A dermoscopic image of a skin lesion:
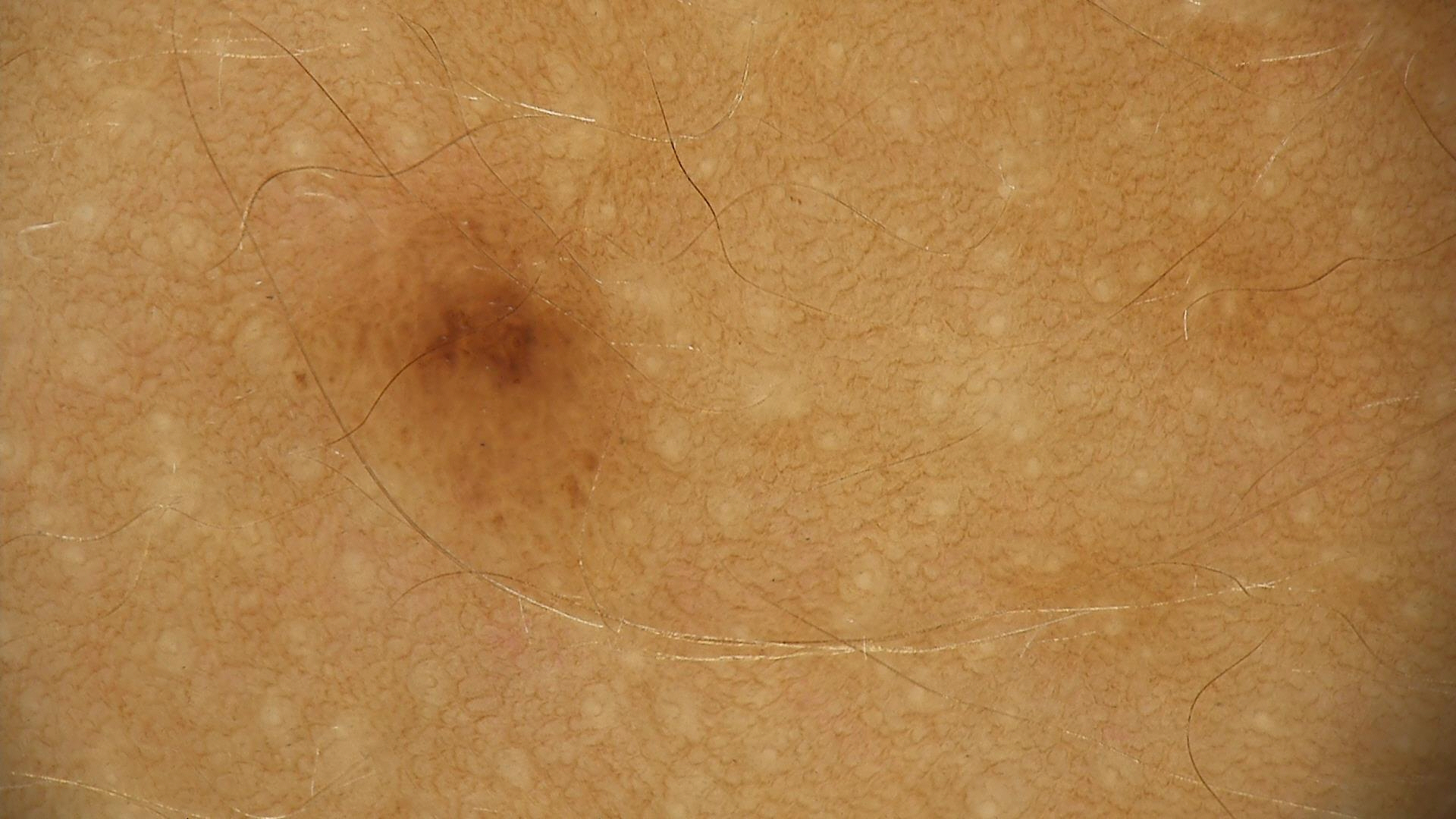Classified as a benign lesion — a dysplastic junctional nevus.